An image taken at a distance — 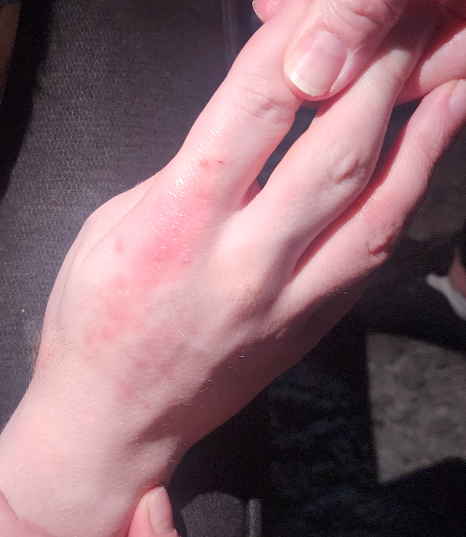{
  "differential": {
    "leading": [
      "Eczema"
    ]
  }
}